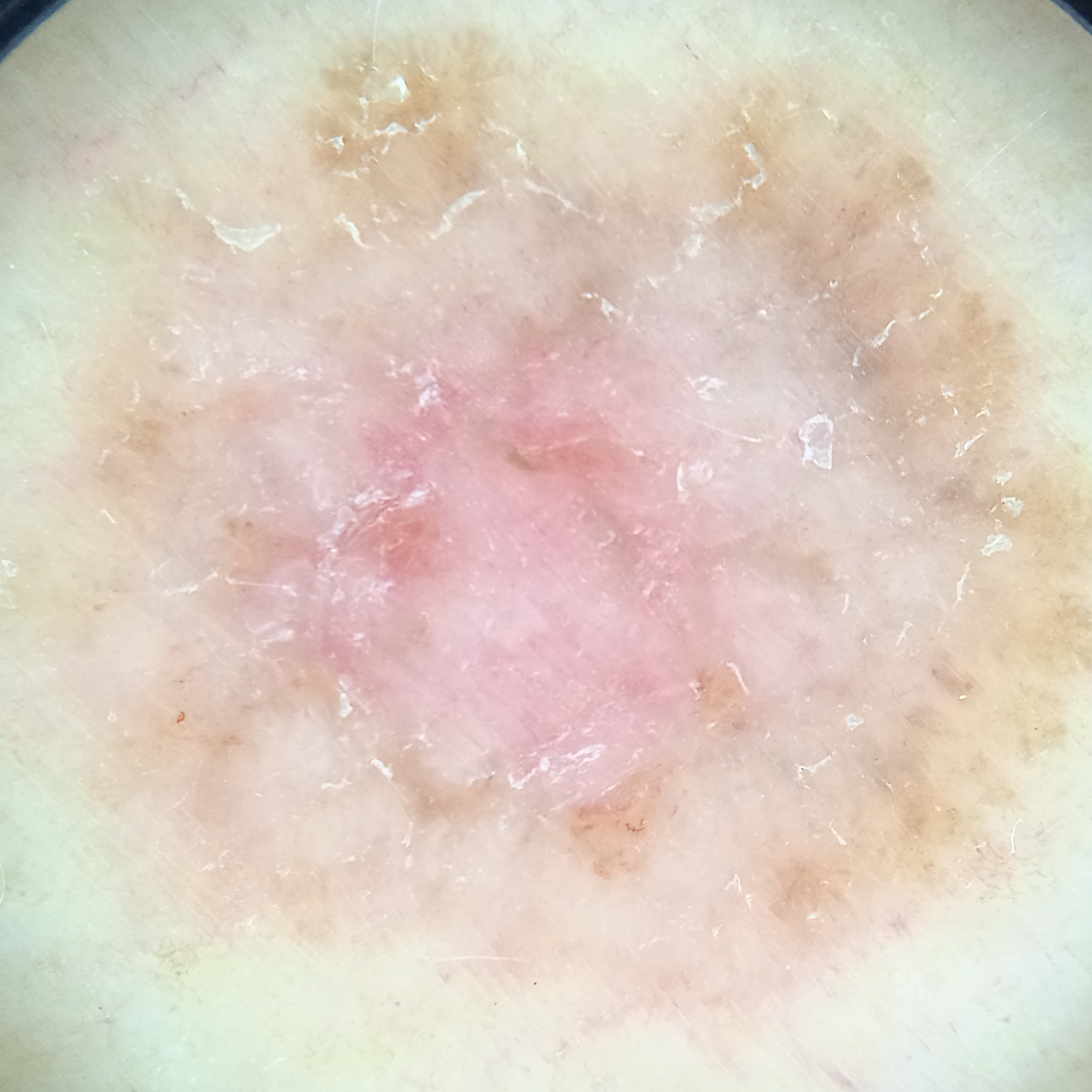{"mole_burden": "few melanocytic nevi overall", "referral": "clinical suspicion of basal cell carcinoma", "sun_reaction": "skin tans without first burning", "image": "dermatoscopic image", "risk_factors": {"positive": ["a personal history of cancer", "a personal history of skin cancer"]}, "diagnosis": {"name": "basal cell carcinoma", "malignancy": "malignant"}}